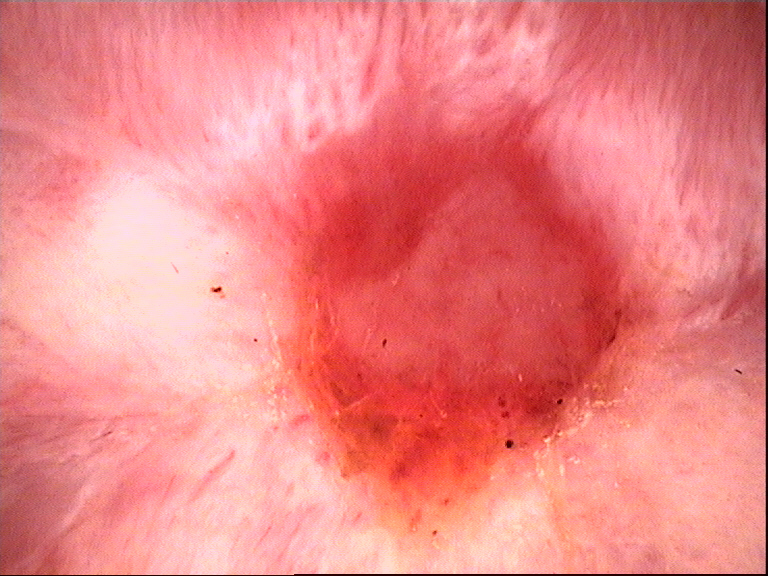A dermoscopy image of a single skin lesion. This is a keratinocytic lesion. Biopsy-confirmed as a squamous cell carcinoma.